A female patient 46 years of age: 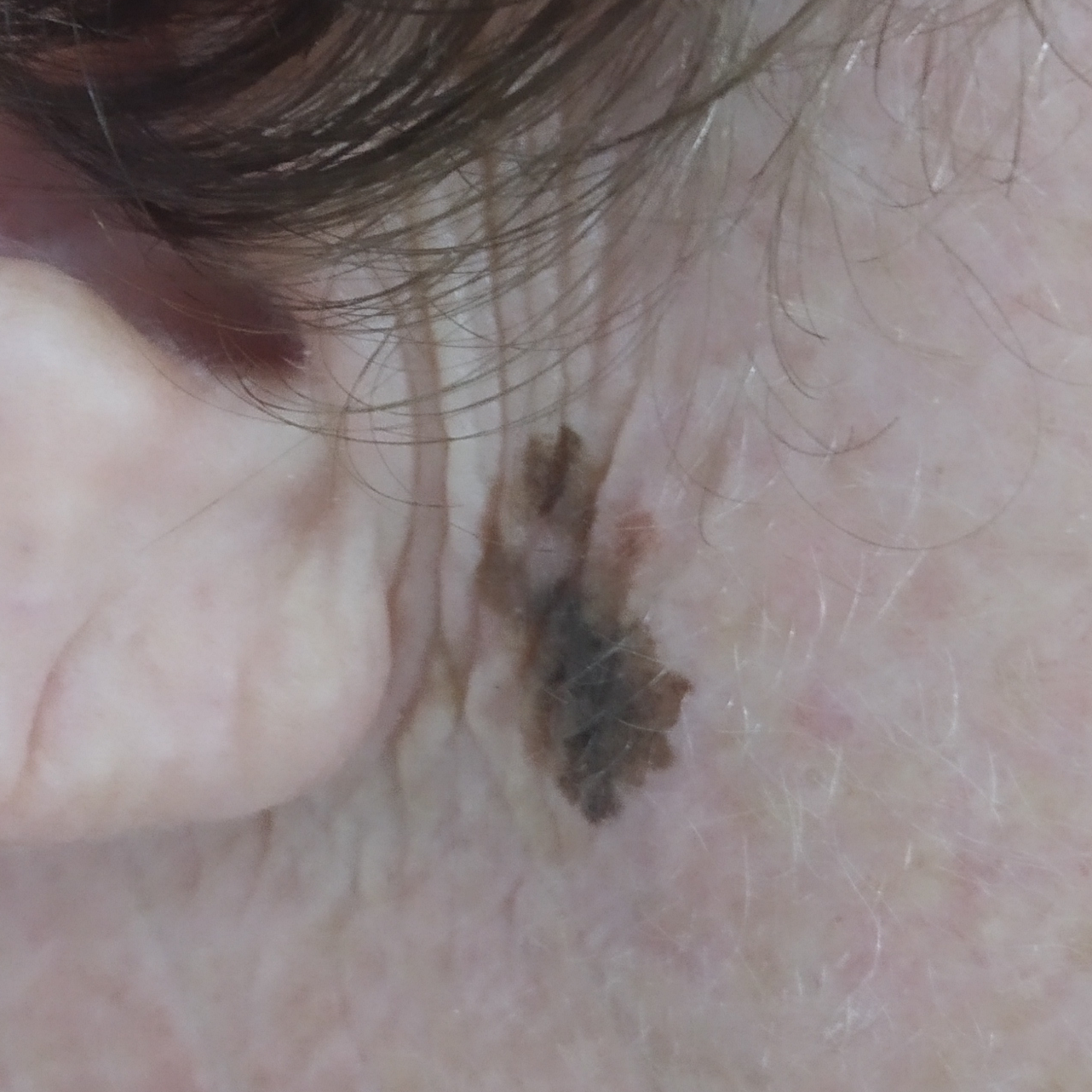location: the face
symptoms: itching, growth, change in appearance
diagnosis: melanoma (biopsy-proven)